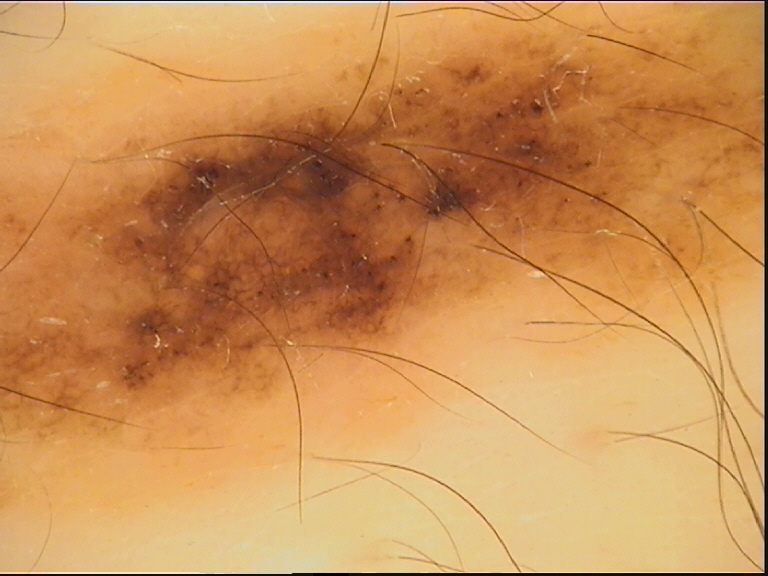Consistent with a dysplastic compound nevus.